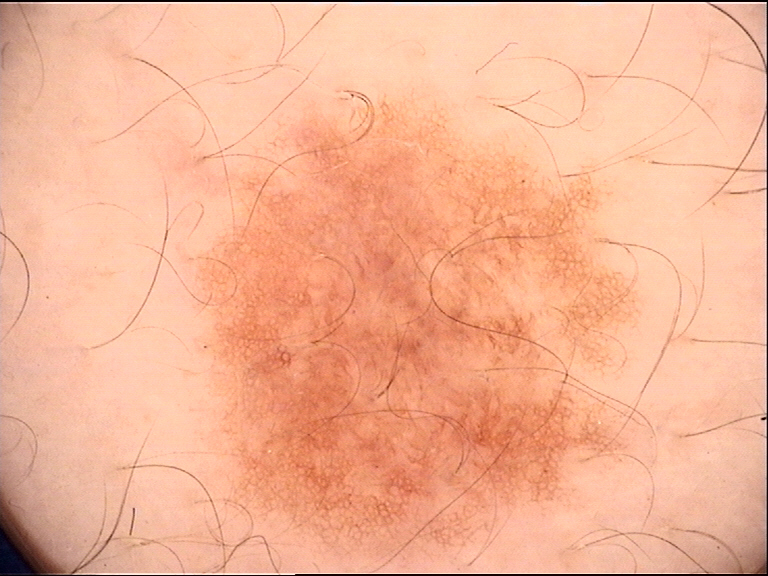Findings: A dermoscopic photograph of a skin lesion. Conclusion: Diagnosed as a benign lesion — a dysplastic junctional nevus.